This is a close-up image: 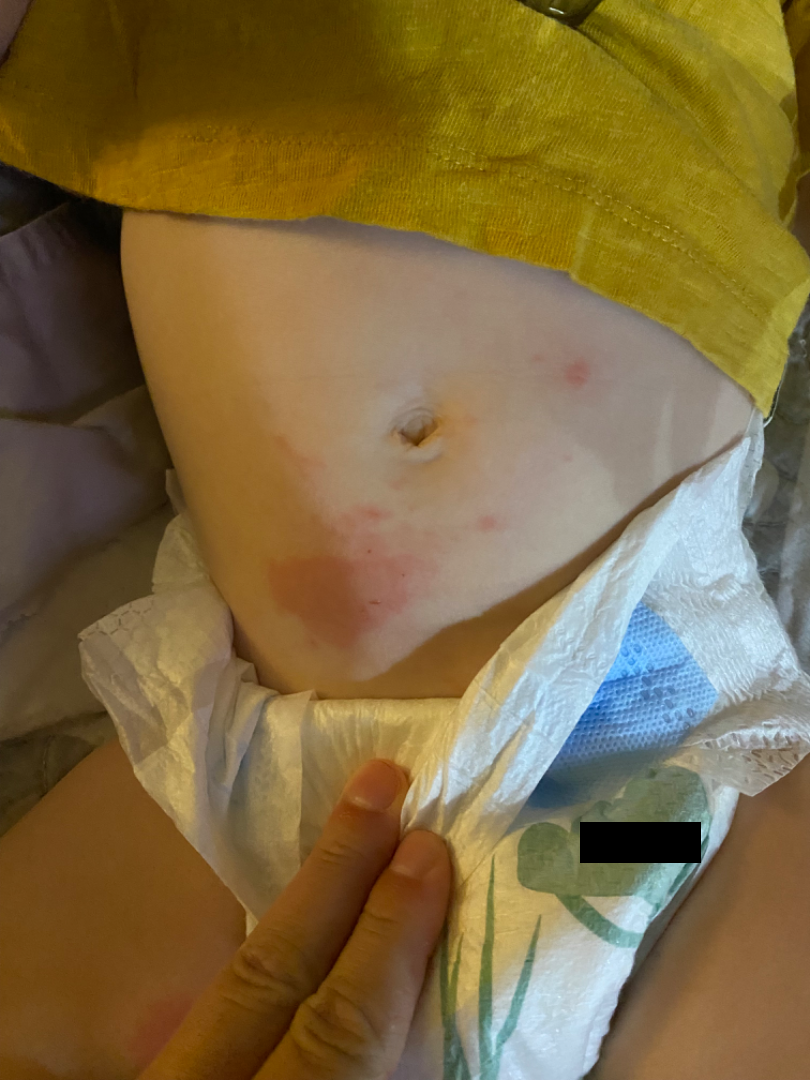The skin findings could not be characterized from the image.
Skin tone: human graders estimated MST 2.